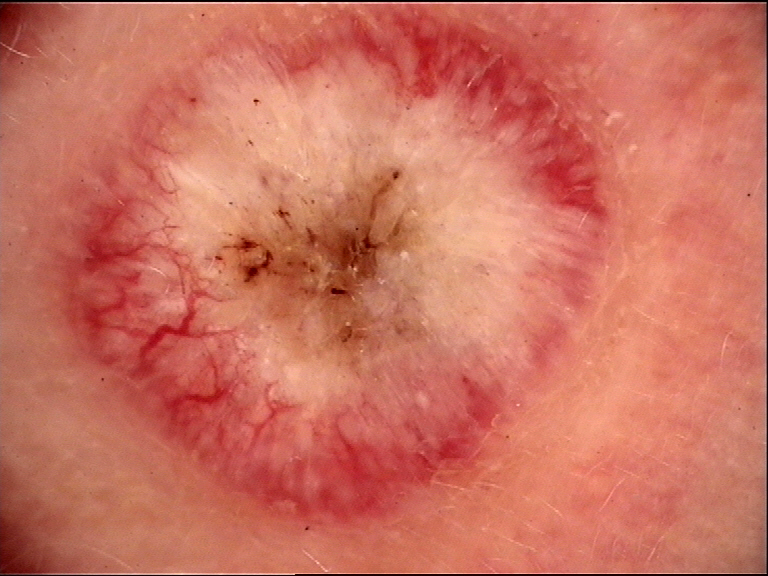A dermatoscopic image of a skin lesion. Confirmed on histopathology as a squamous cell carcinoma.